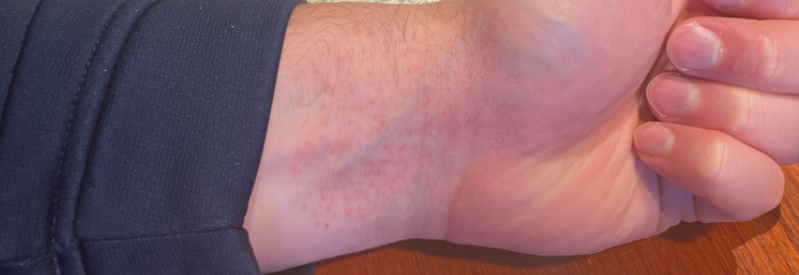Eczema (most likely); Lichen planus/lichenoid eruption (considered).